An image taken at a distance.
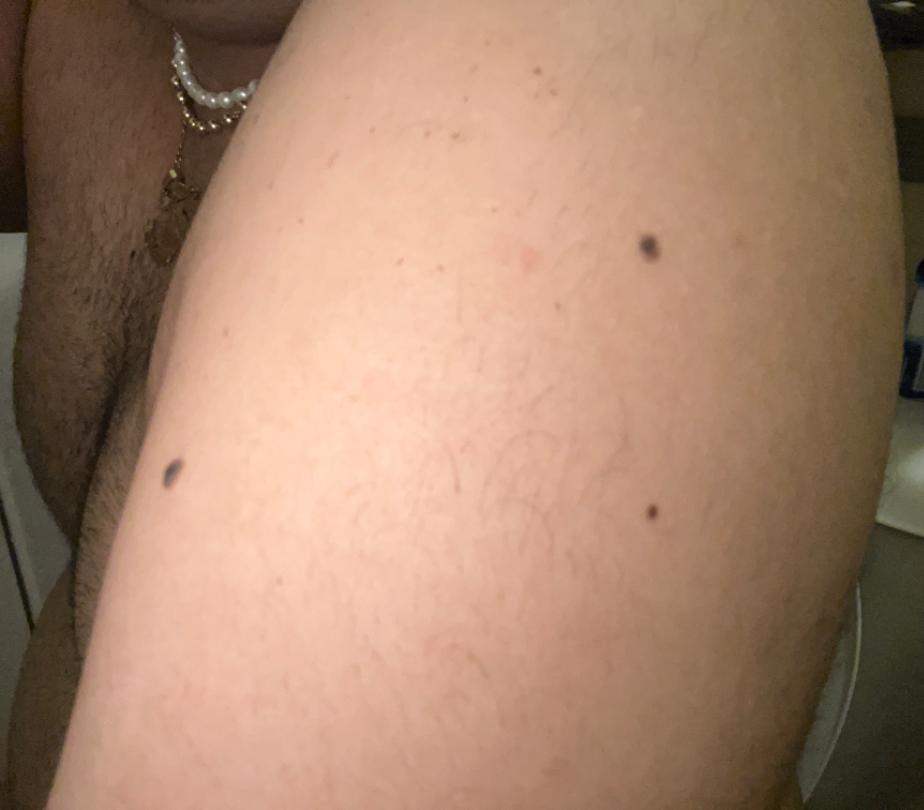Q: What was the assessment?
A: could not be assessed